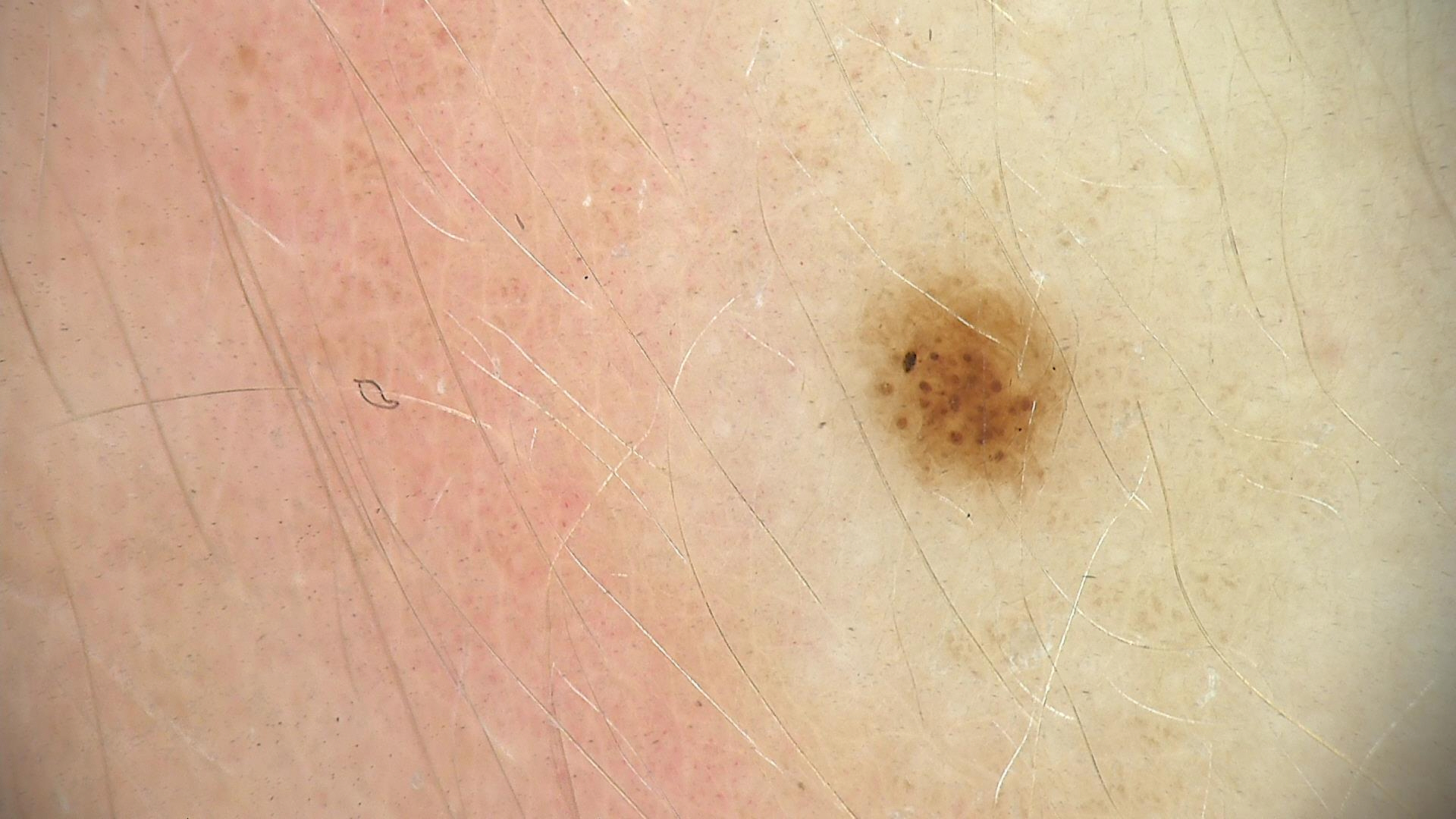A dermoscopic close-up of a skin lesion.
Consistent with a dysplastic junctional nevus.